The contributor is 60–69, female · the leg is involved · a close-up photograph:
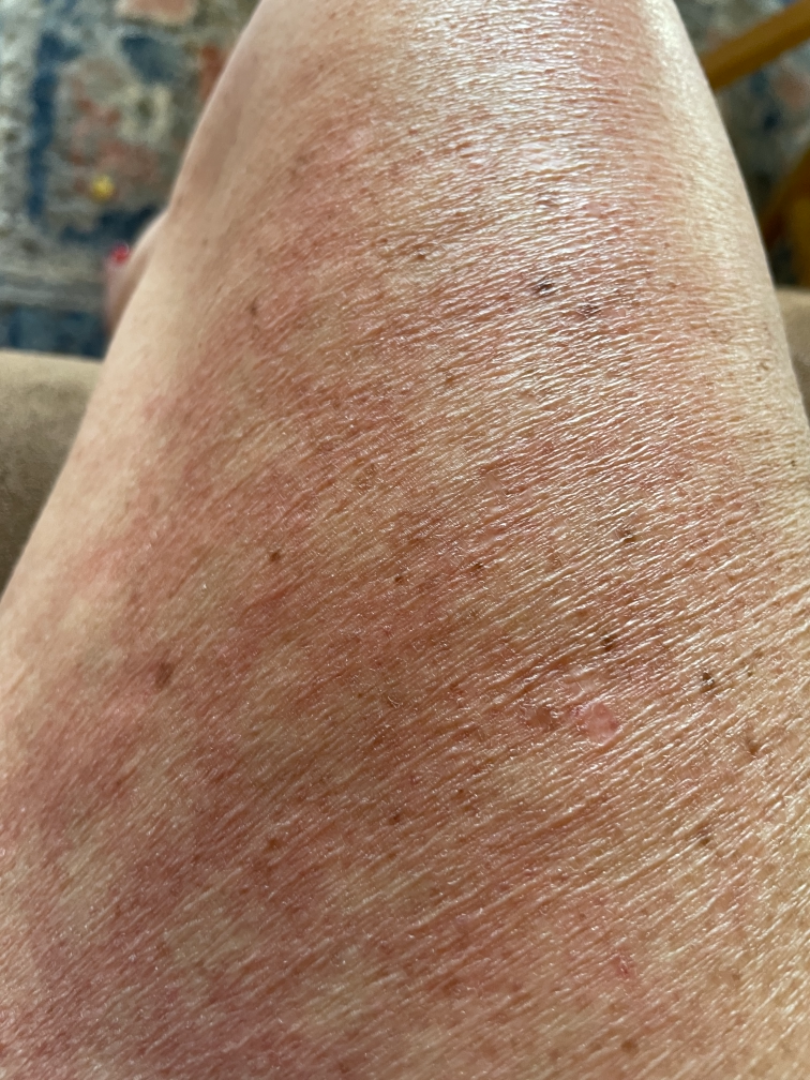assessment=could not be assessed